A clinical close-up photograph of a skin lesion. A subject age 71 — 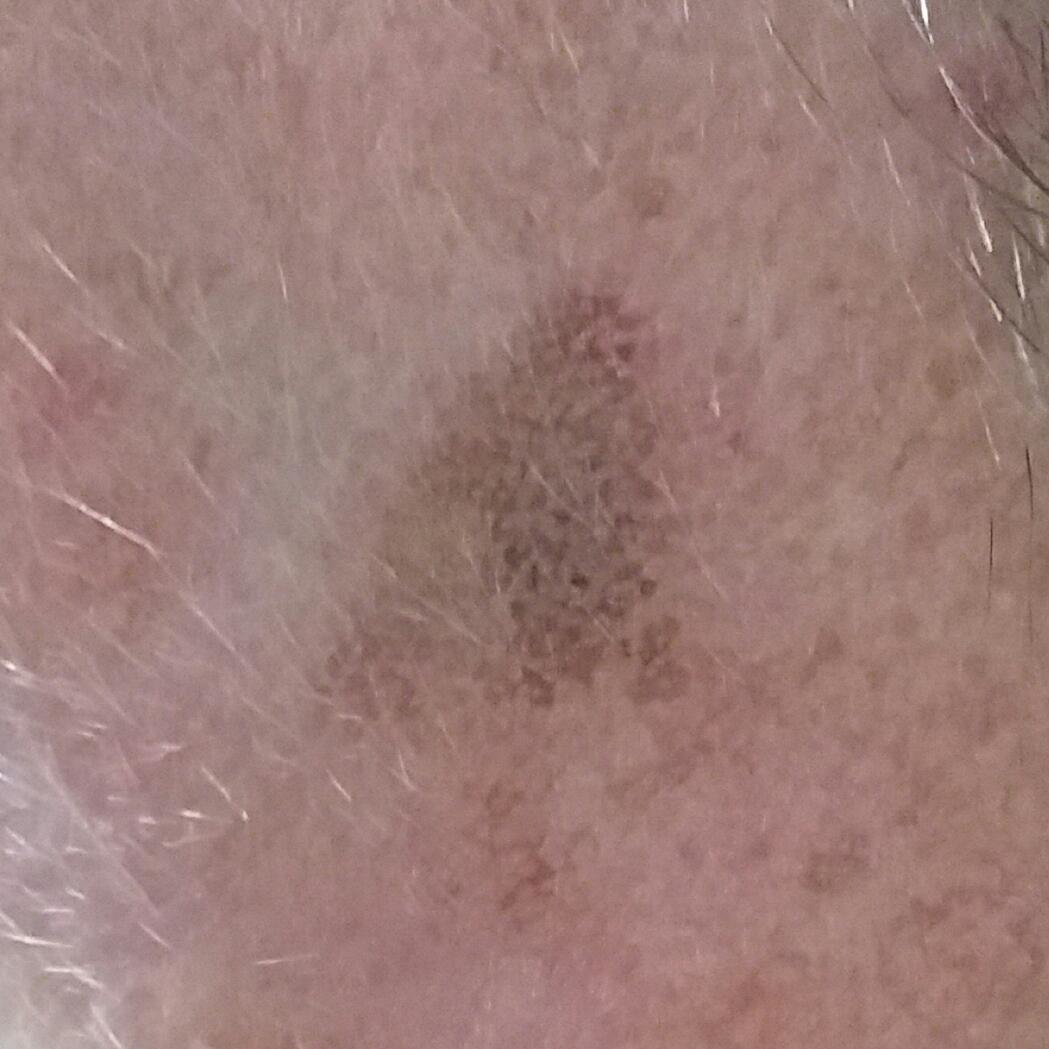Patient and lesion:
The patient reports no symptoms.
Impression:
Expert review favored a benign skin lesion — a seborrheic keratosis.